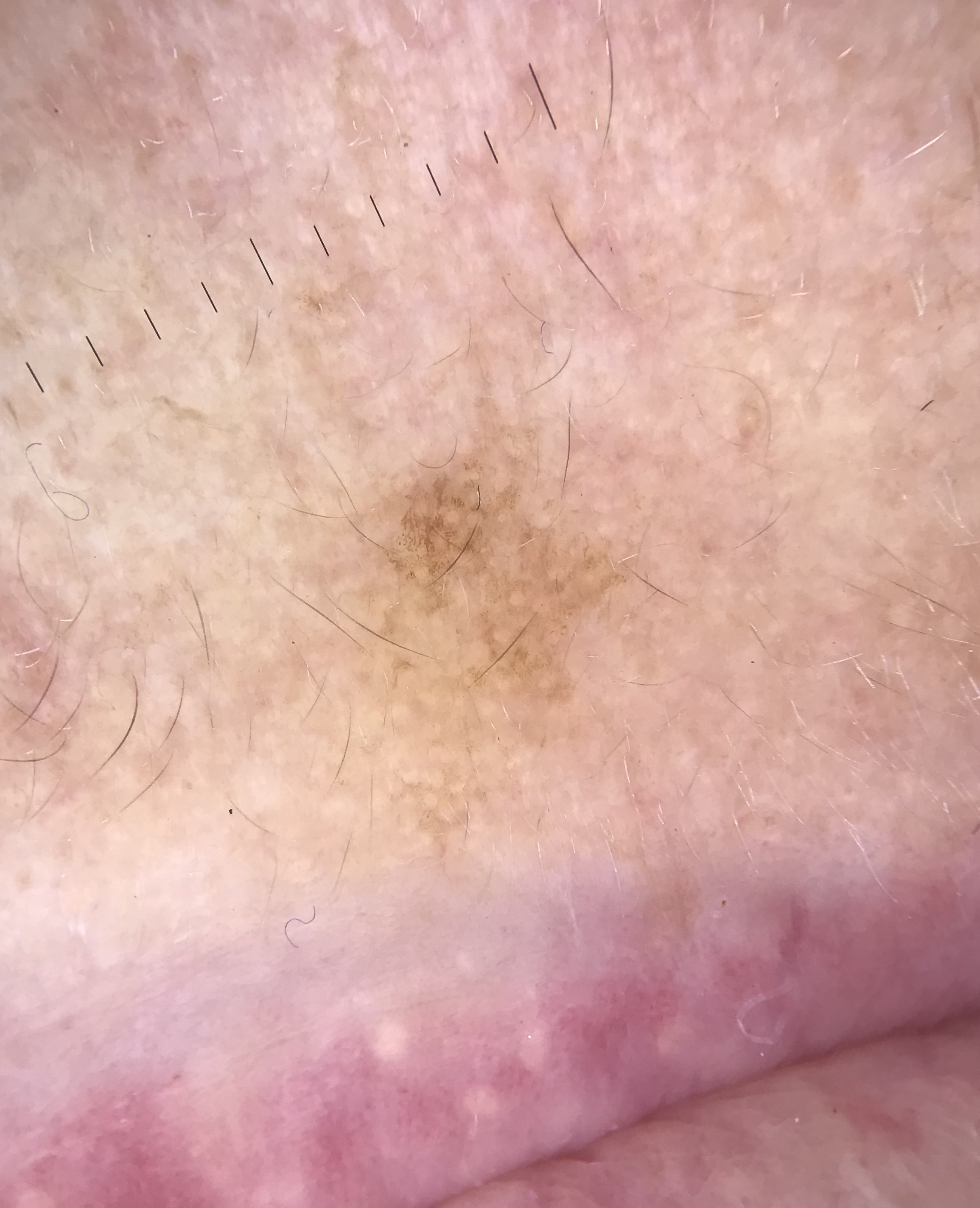Findings:
A dermatoscopic image of a skin lesion.
Impression:
The diagnosis was a solar lentigo.